Close-up view. Texture is reported as rough or flaky, raised or bumpy and fluid-filled. The lesion involves the sole of the foot, leg, top or side of the foot, back of the torso, front of the torso, head or neck and arm. Associated systemic symptoms include fatigue and joint pain. Self-categorized by the patient as a rash. The lesion is associated with itching, burning, pain, bleeding, bothersome appearance and enlargement.
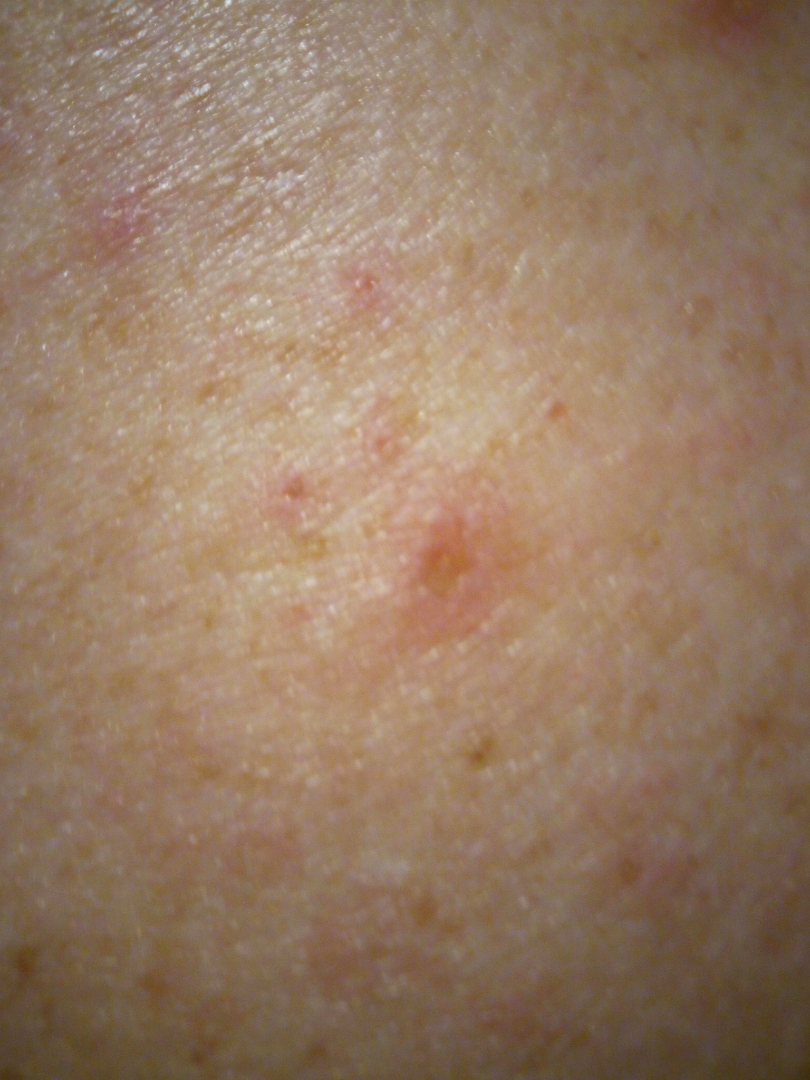assessment — unable to determine.